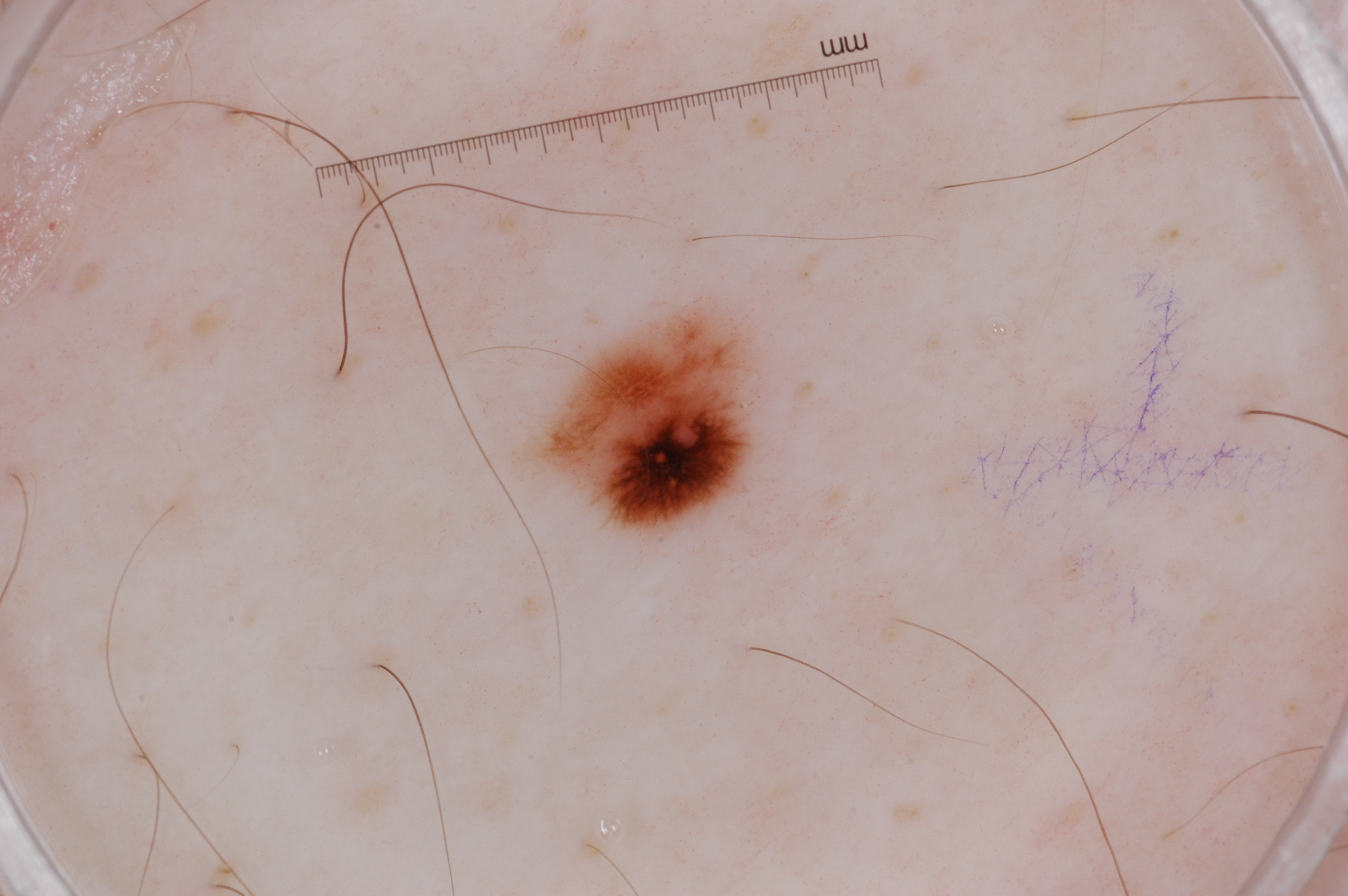| key | value |
|---|---|
| image | dermoscopic image |
| patient | male, roughly 45 years of age |
| dermoscopic findings | pigment network and negative network |
| location | <box>537, 308, 758, 532</box> |
| diagnosis | a melanoma, a malignancy |